A dermatoscopic image of a skin lesion: 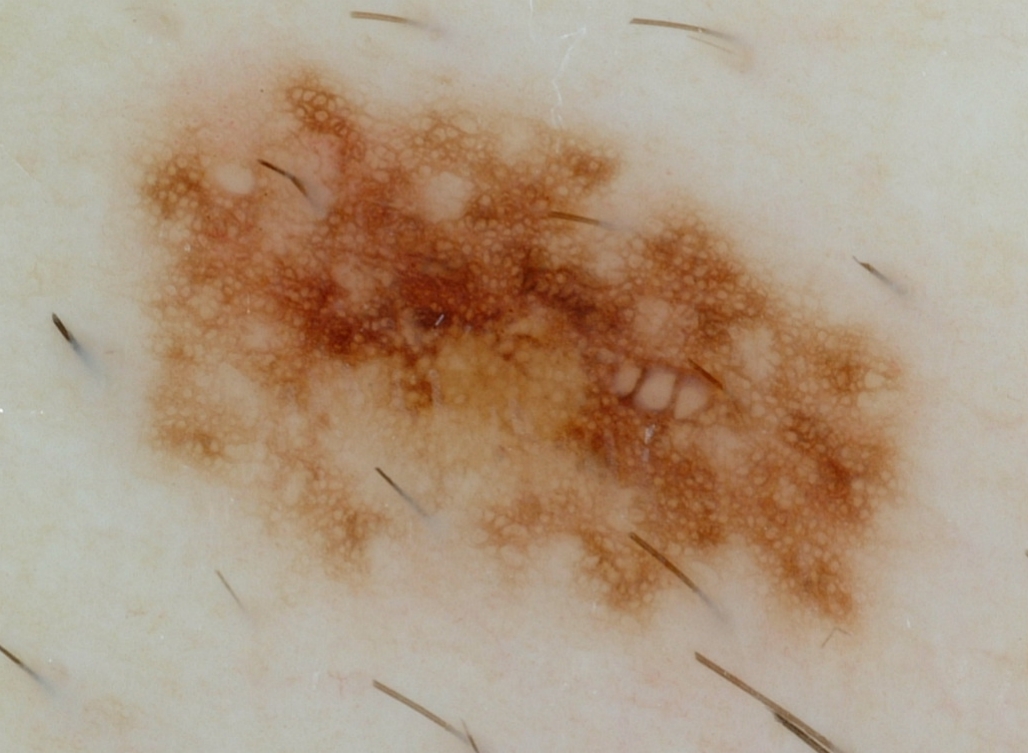Dermoscopic review identifies pigment network; no globules, milia-like cysts, negative network, or streaks.
In (x1, y1, x2, y2) order, the lesion's extent is <bbox>131, 64, 907, 638</bbox>.
A prominent lesion filling much of the field.
Clinically diagnosed as a melanocytic nevus.